A skin lesion imaged with contact-polarized dermoscopy.
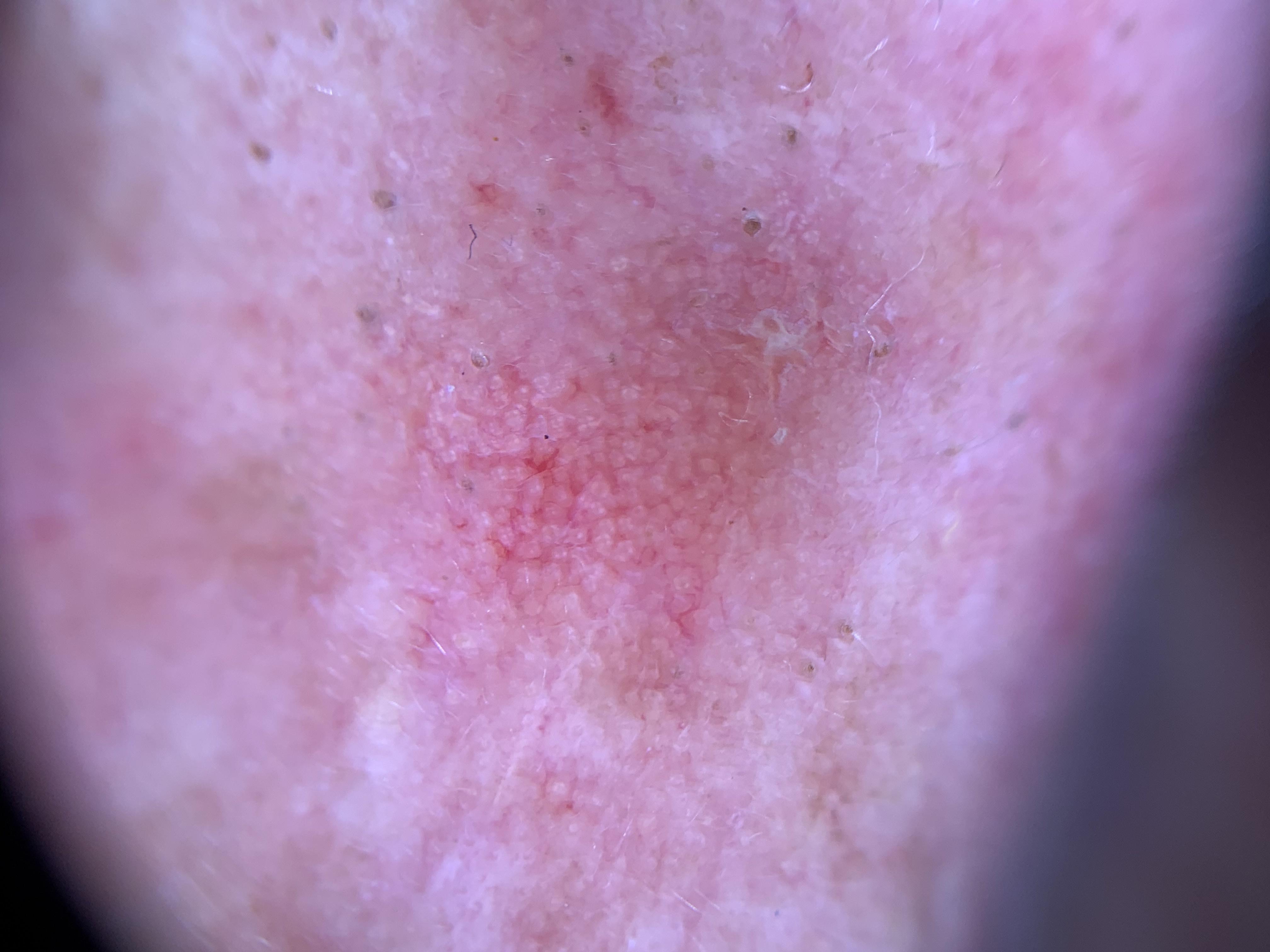The lesion is on the head or neck.
The clinical assessment was a solar or actinic keratosis.